Dermoscopy of a skin lesion:
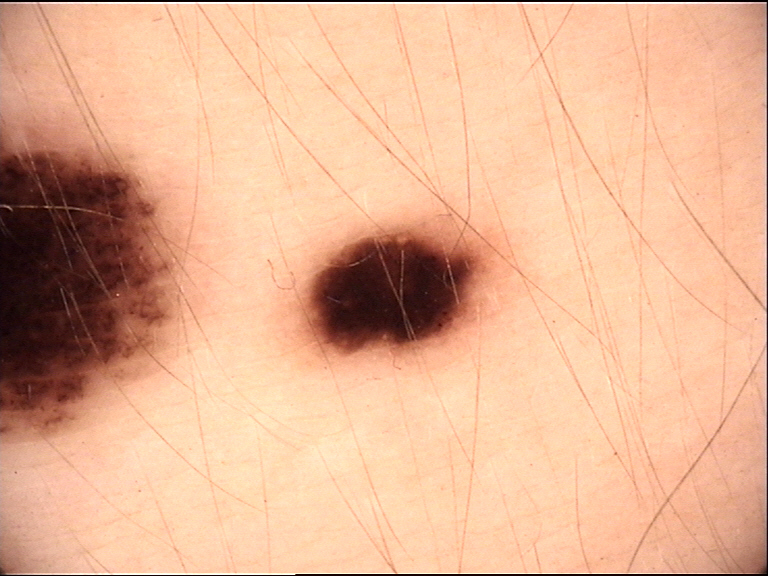Diagnosed as a dysplastic junctional nevus.